This image was taken at a distance; the patient considered this skin that appeared healthy to them; present for less than one week; the patient indicates the lesion is fluid-filled and raised or bumpy; the patient also reports fatigue and fever: 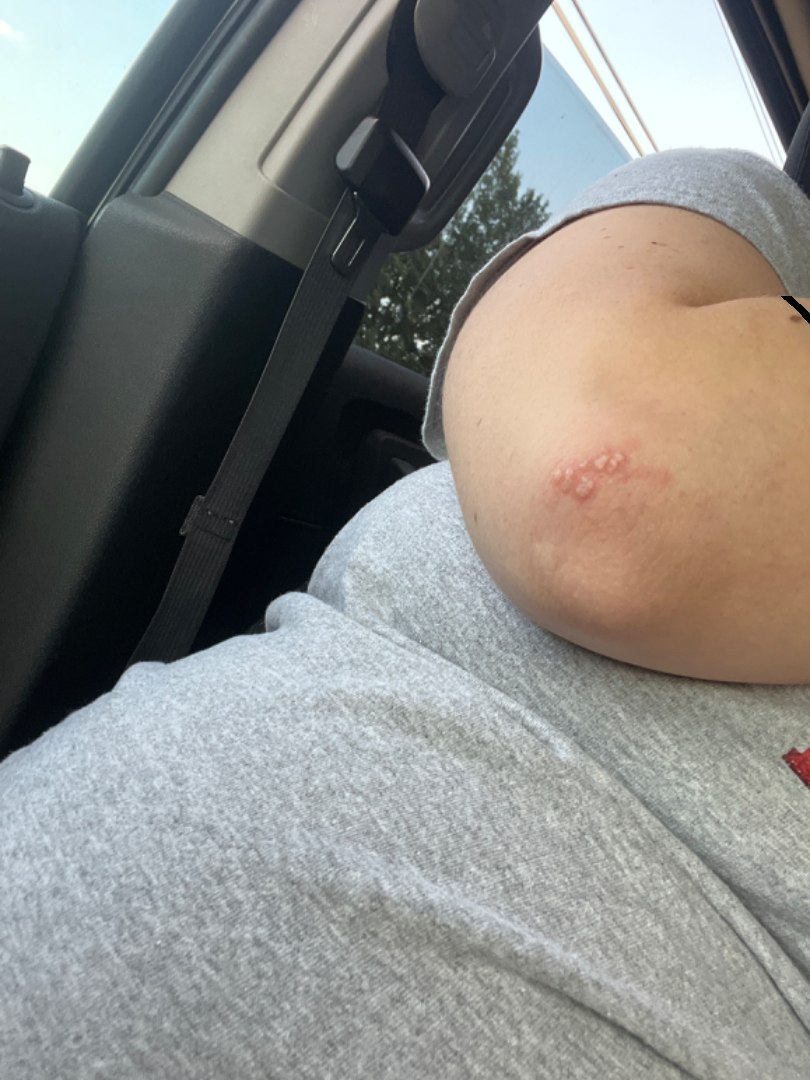* assessment: most likely Herpes Simplex; also on the differential is Impetigo; possibly Herpes Zoster